The back of the hand and leg are involved. Close-up view: 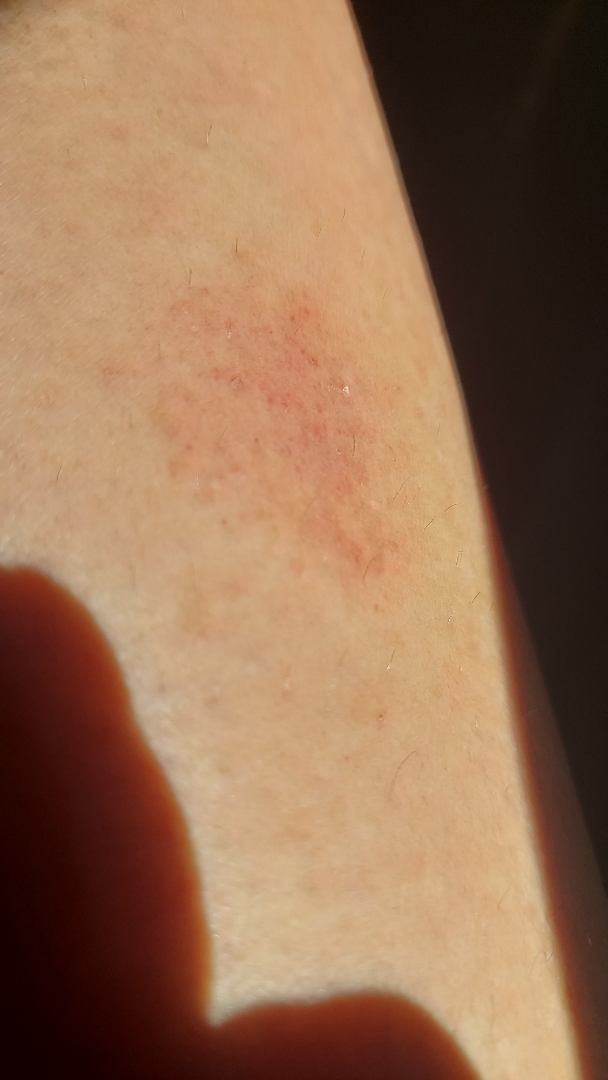lesion texture=raised or bumpy | lesion symptoms=enlargement | patient describes the issue as=a rash | present for=one to four weeks | skin tone=Fitzpatrick phototype II | clinical impression=the favored diagnosis is Pigmented purpuric eruption; also on the differential is Tinea; possibly Eczema.